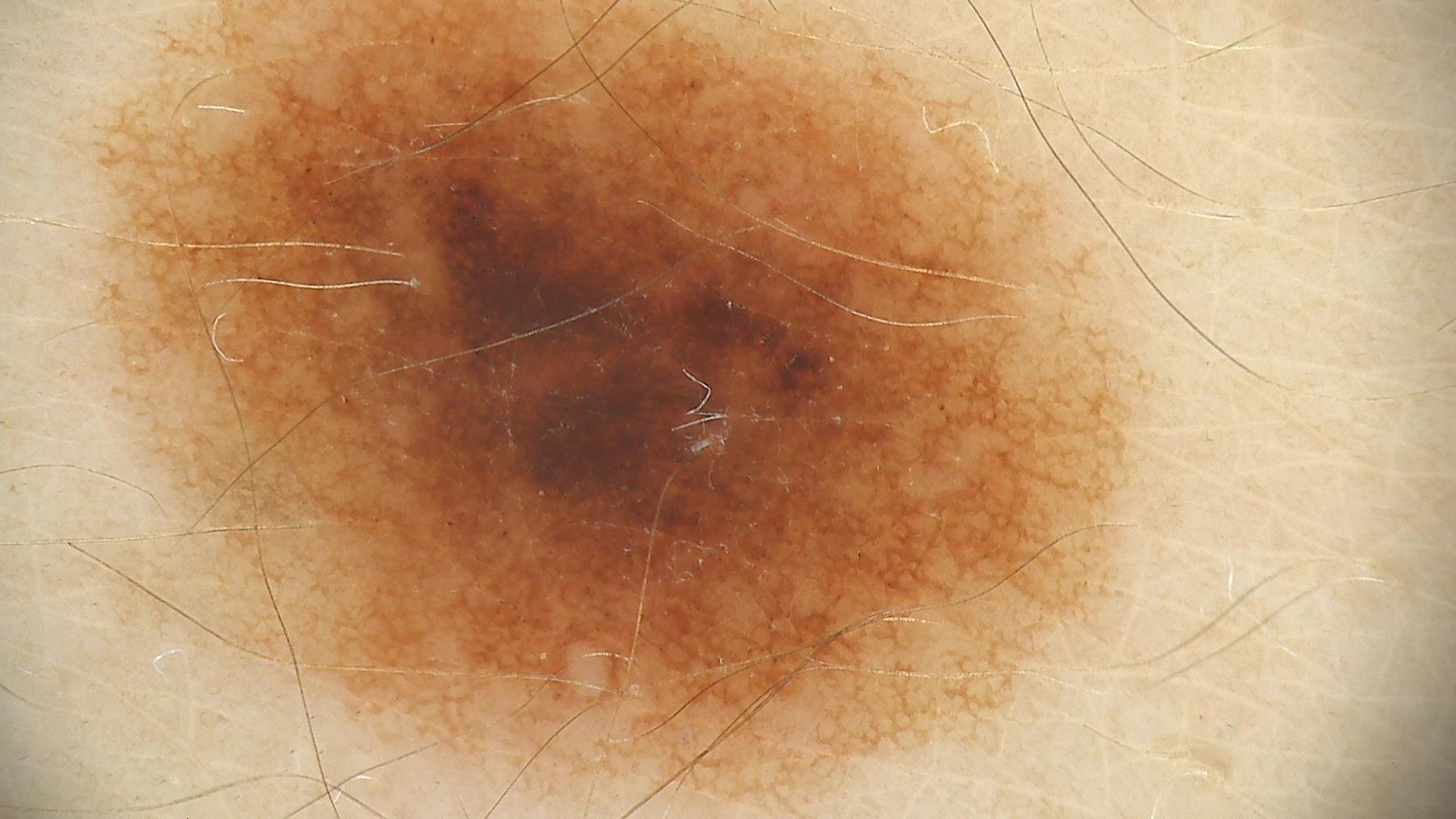A dermoscopic photograph of a skin lesion. The diagnosis was a dysplastic junctional nevus.